A dermatoscopic image of a skin lesion.
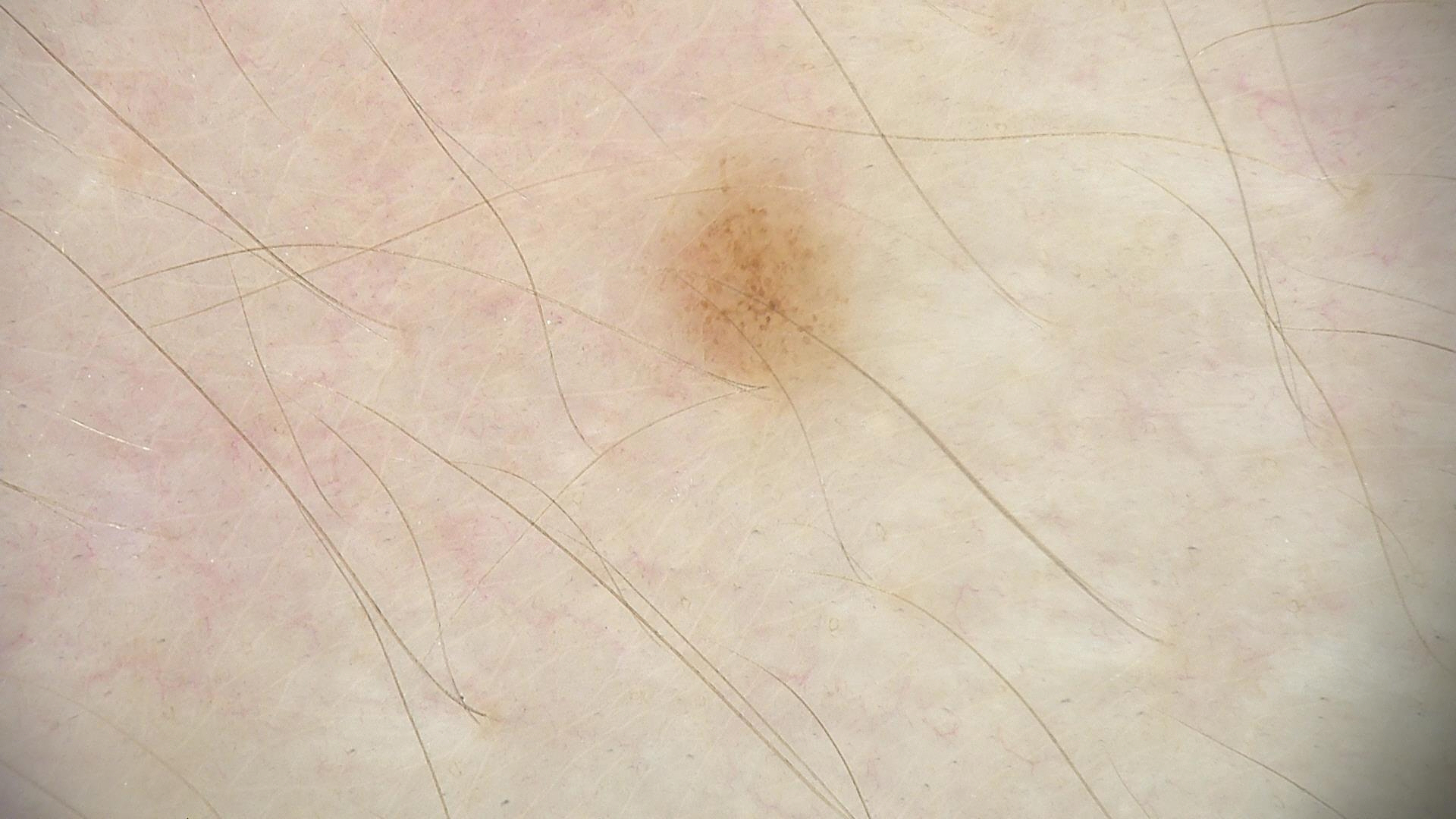Labeled as a dysplastic junctional nevus.